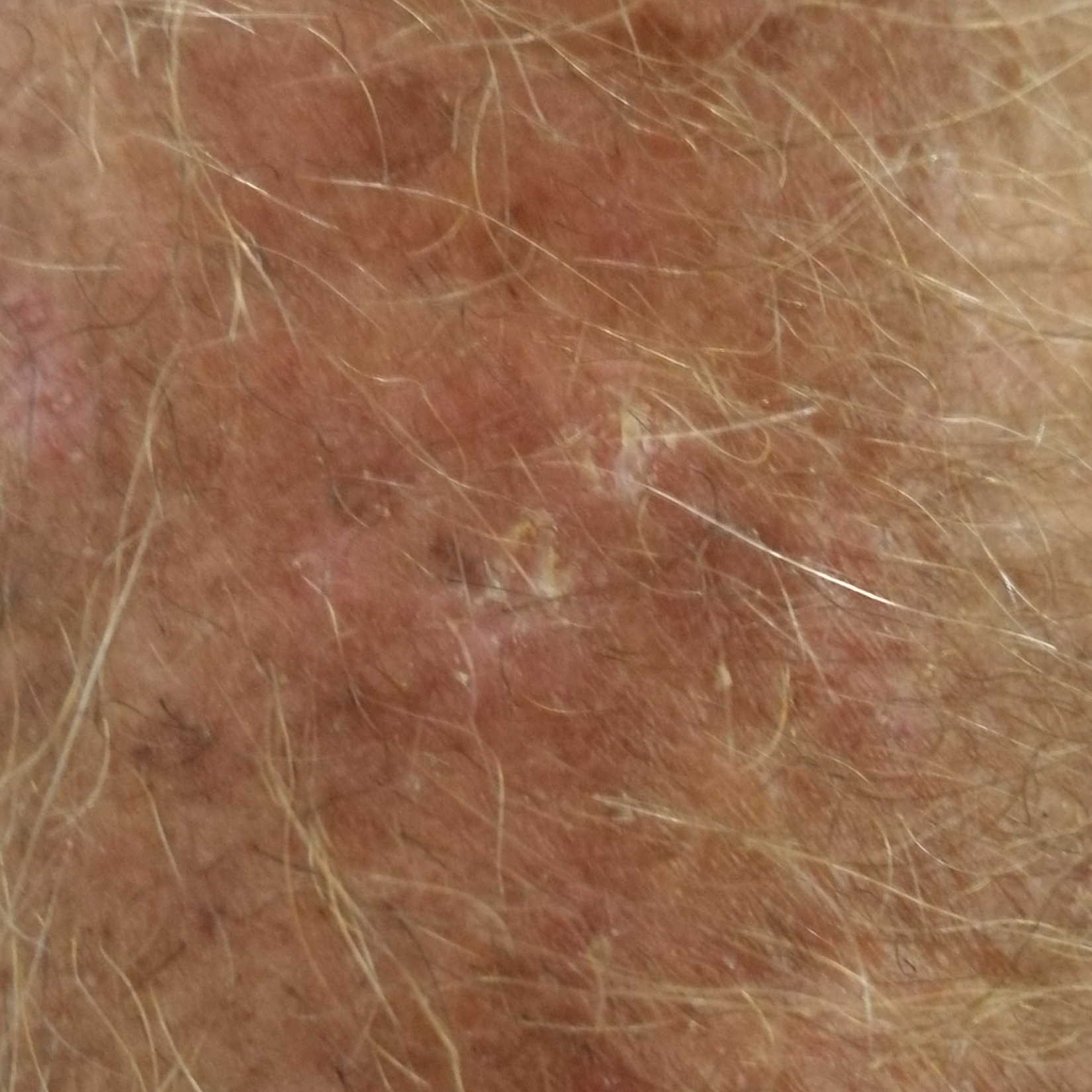A subject in their late 60s.
A clinical photo of a skin lesion taken with a smartphone.
The lesion involves a forearm.
By the patient's account, the lesion itches, but has not bled and does not hurt.
Consistent with an actinic keratosis.